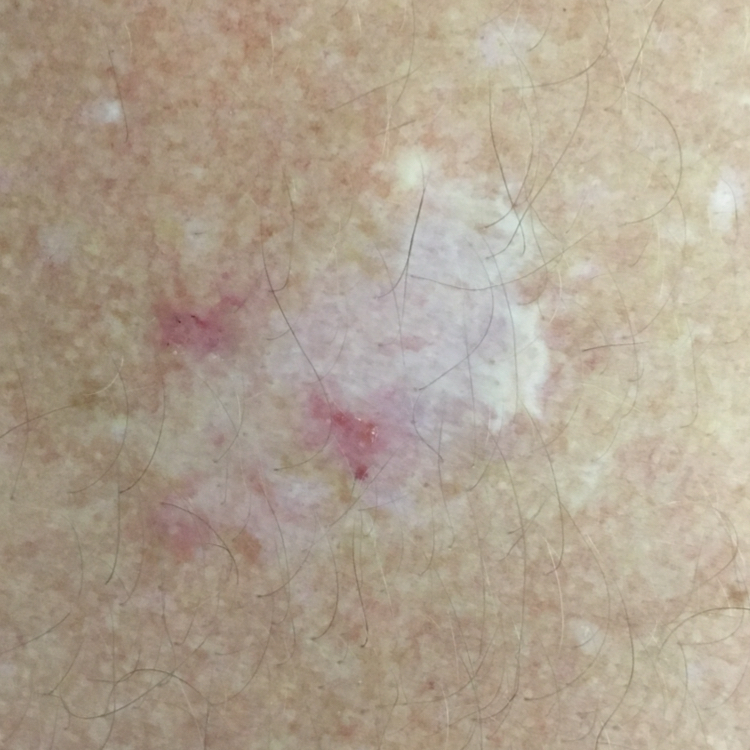Confirmed on histopathology as a basal cell carcinoma.